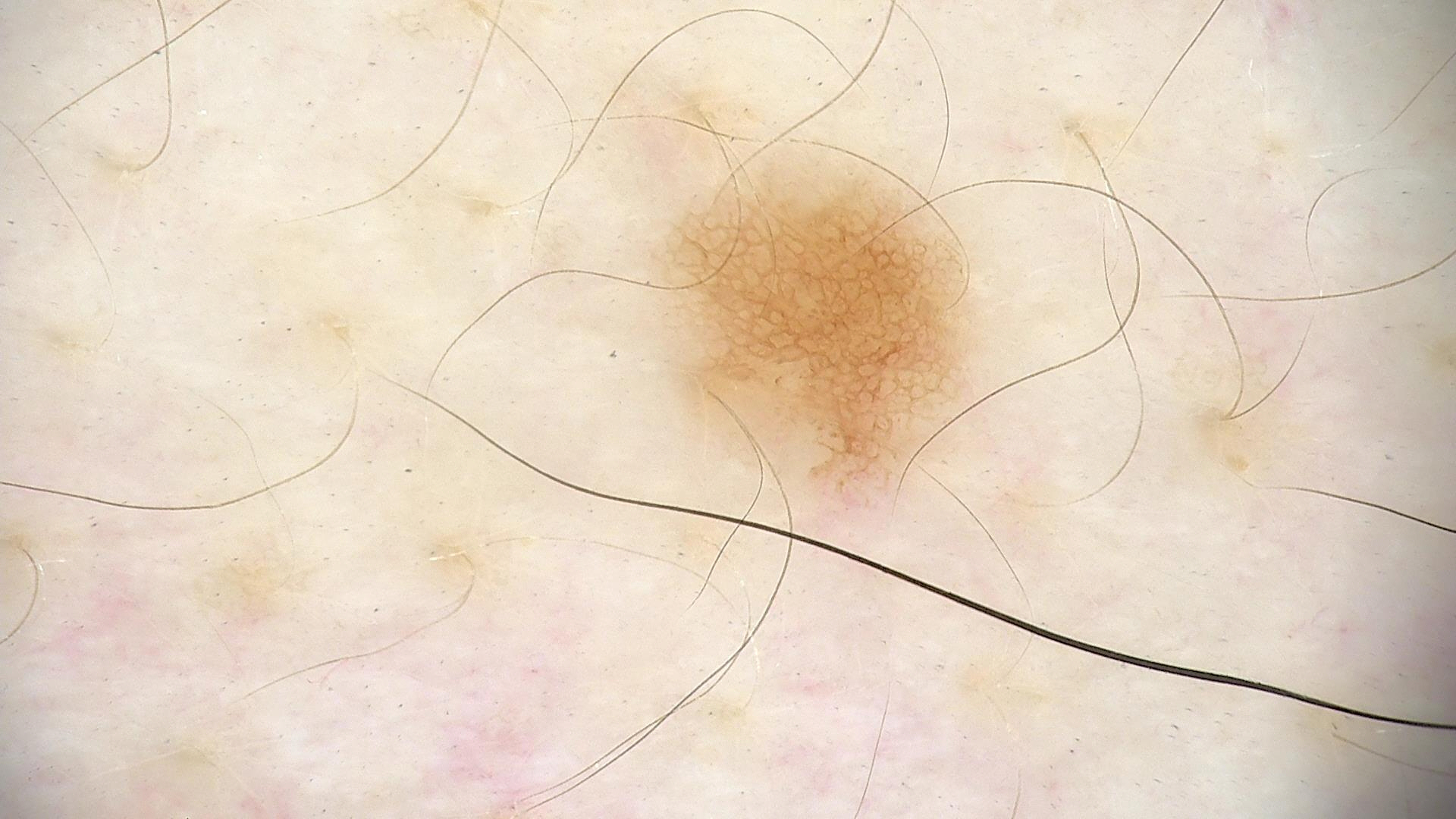imaging = dermatoscopy, class = junctional nevus (expert consensus).